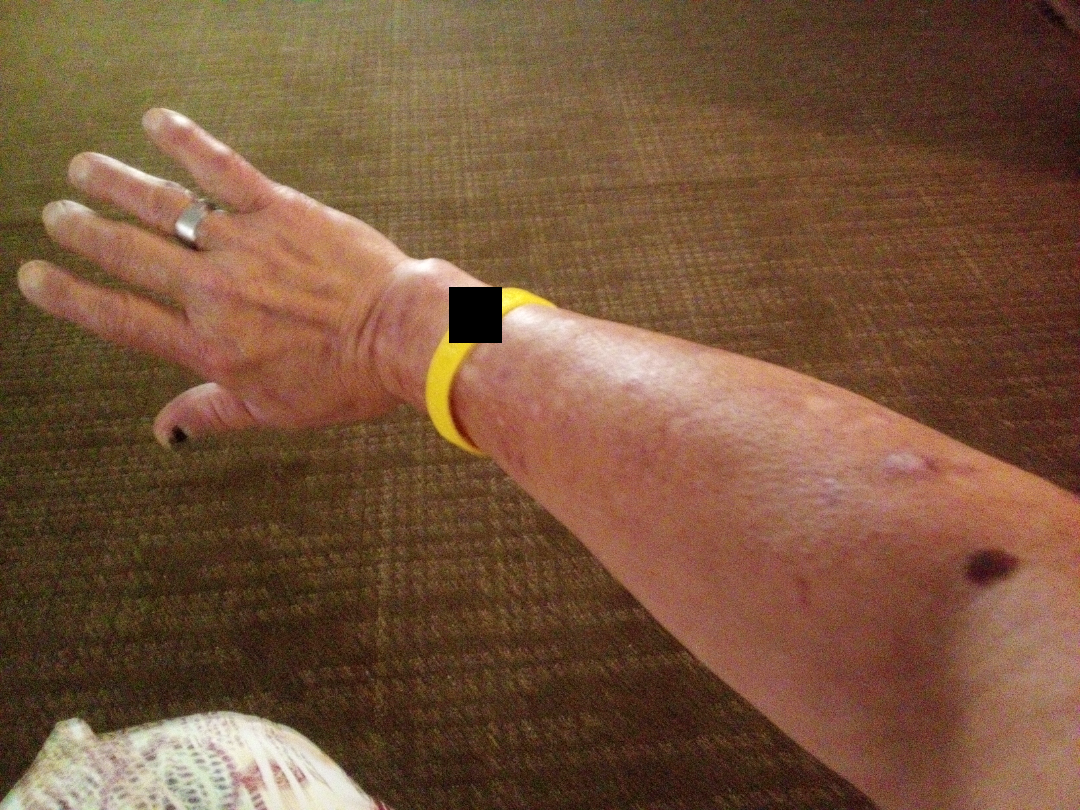Notes:
- assessment: ungradable on photographic review
- photo taken: at a distance
- reported symptoms: darkening, itching, pain and bothersome appearance
- body site: arm
- patient describes the issue as: a rash
- patient: female, age 50–59